A dermatoscopic image of a skin lesion.
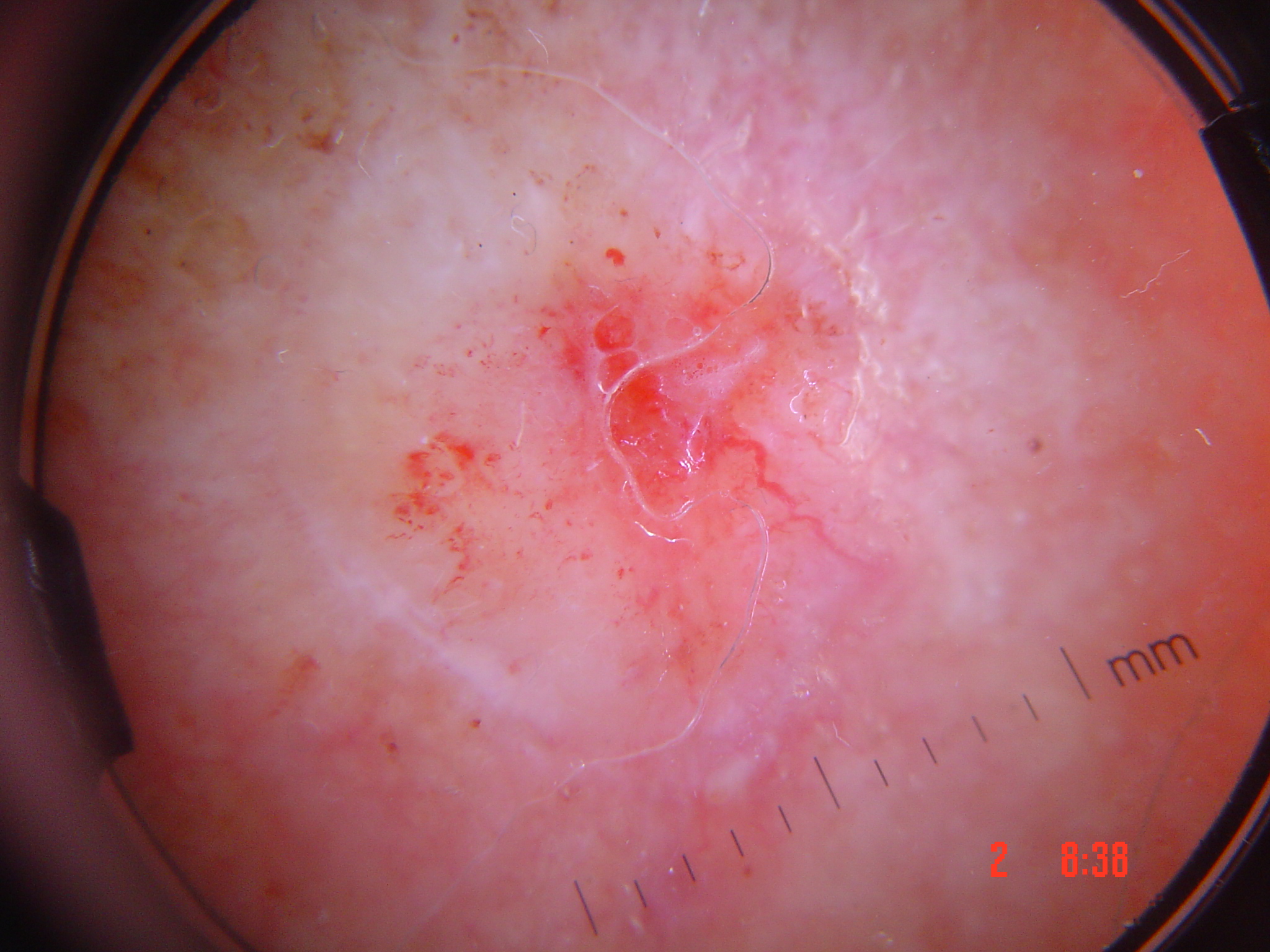Histopathologically confirmed as a keratinocytic, malignant lesion — a squamous cell carcinoma.